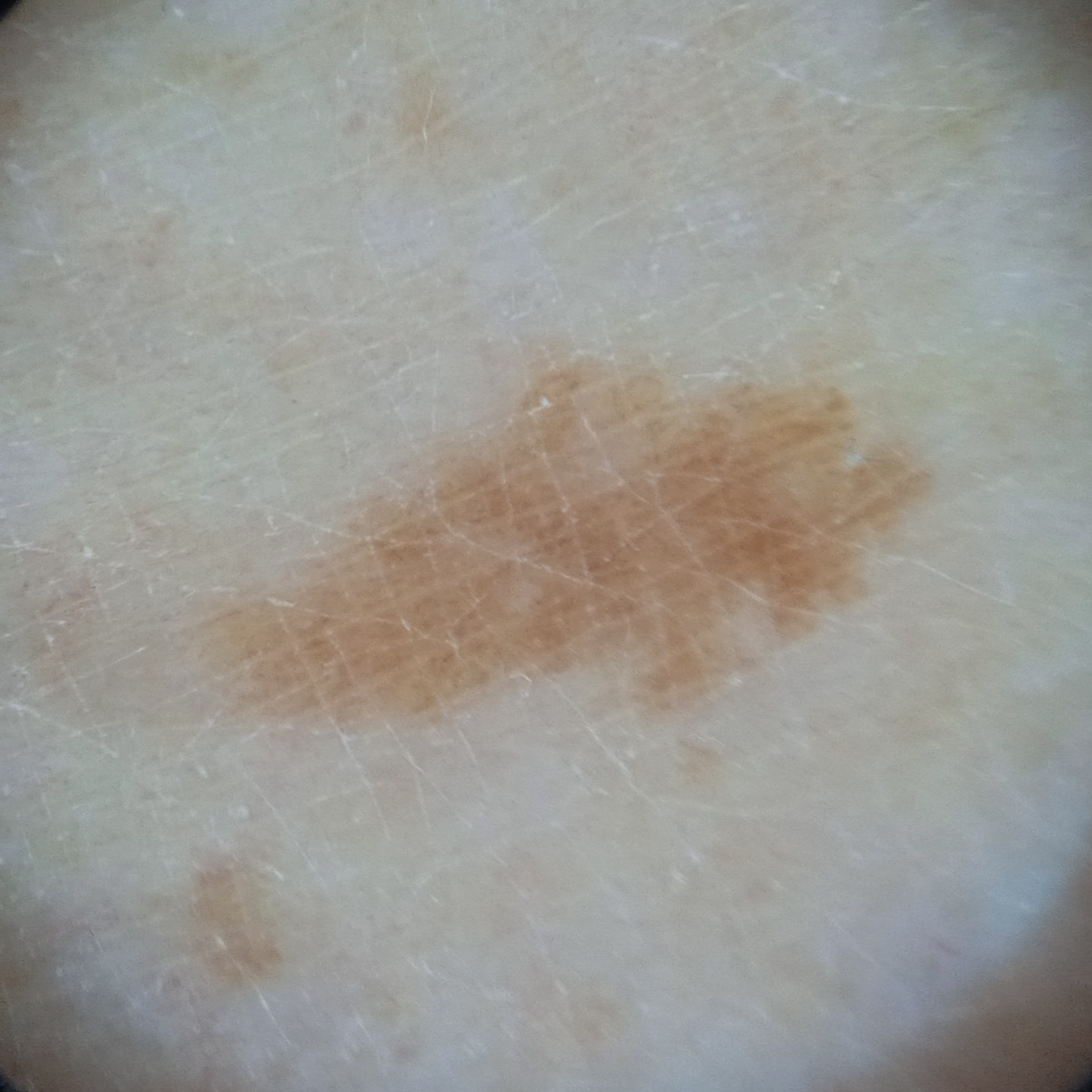Assessment:
Reviewed by four dermatologists, the consensus diagnosis was a melanocytic nevus.